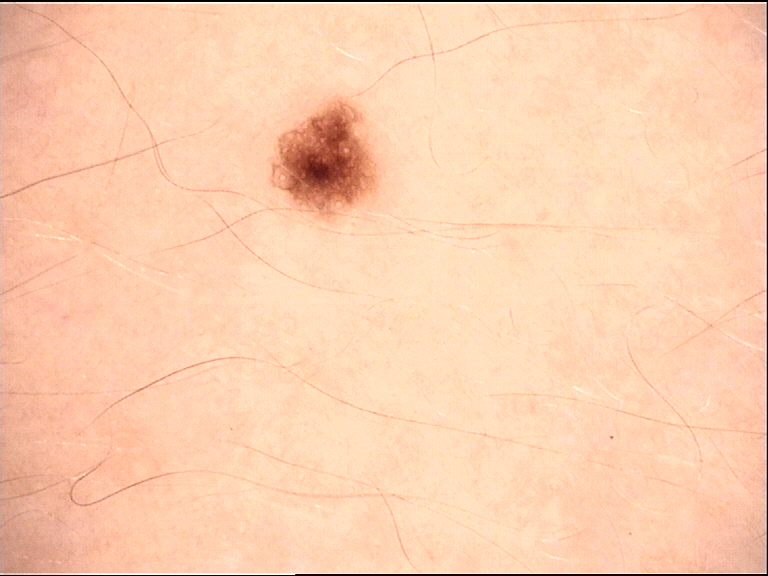A dermoscopic photograph of a skin lesion. The diagnosis was a banal lesion — a junctional nevus.